A male patient in their early 60s. A clinical close-up photograph of a skin lesion. History notes alcohol use and prior malignancy (patient or family). Skin type II: 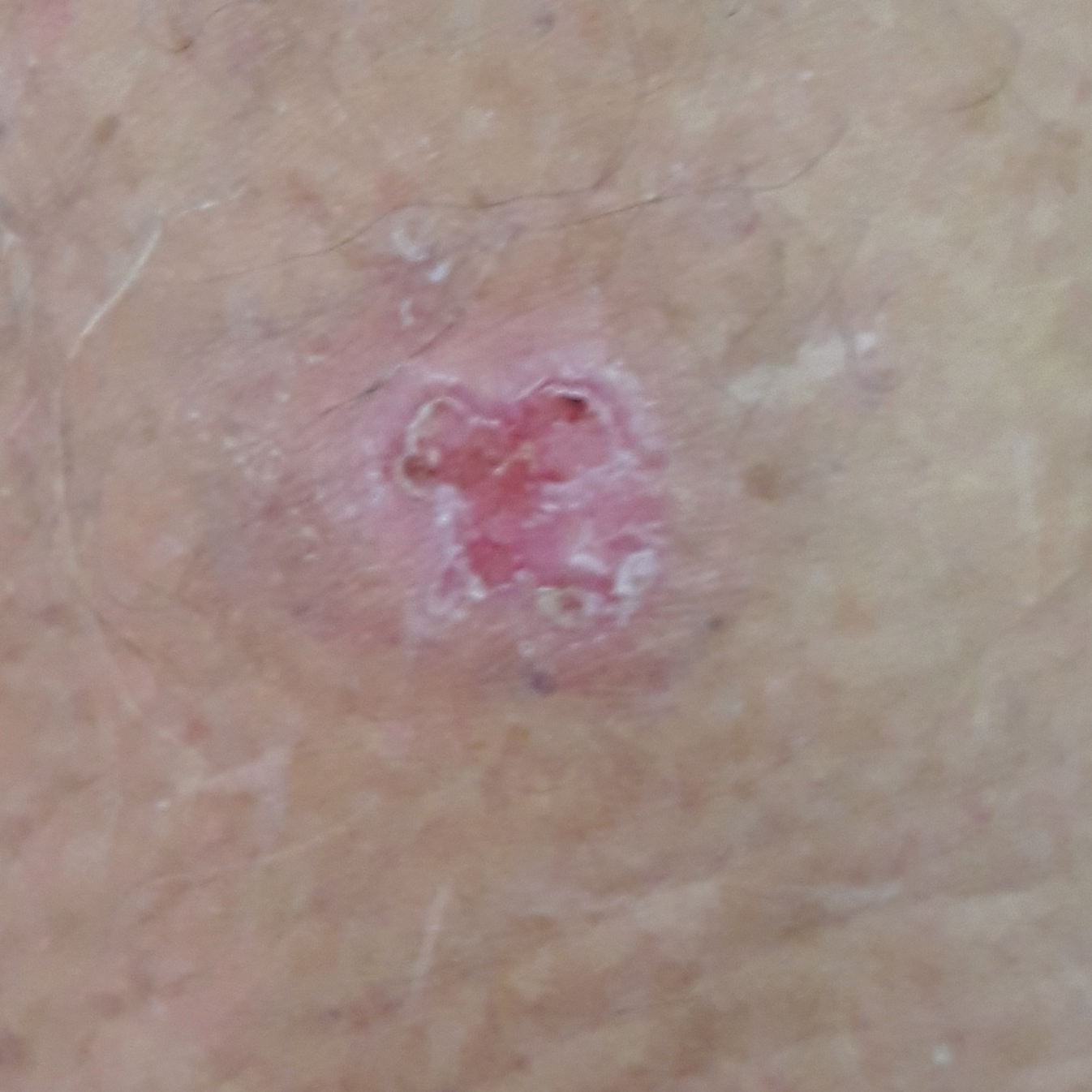region=an arm; size=11 × 9 mm; symptoms=pain, bleeding, growth, elevation, itching / no change in appearance; pathology=basal cell carcinoma (biopsy-proven).